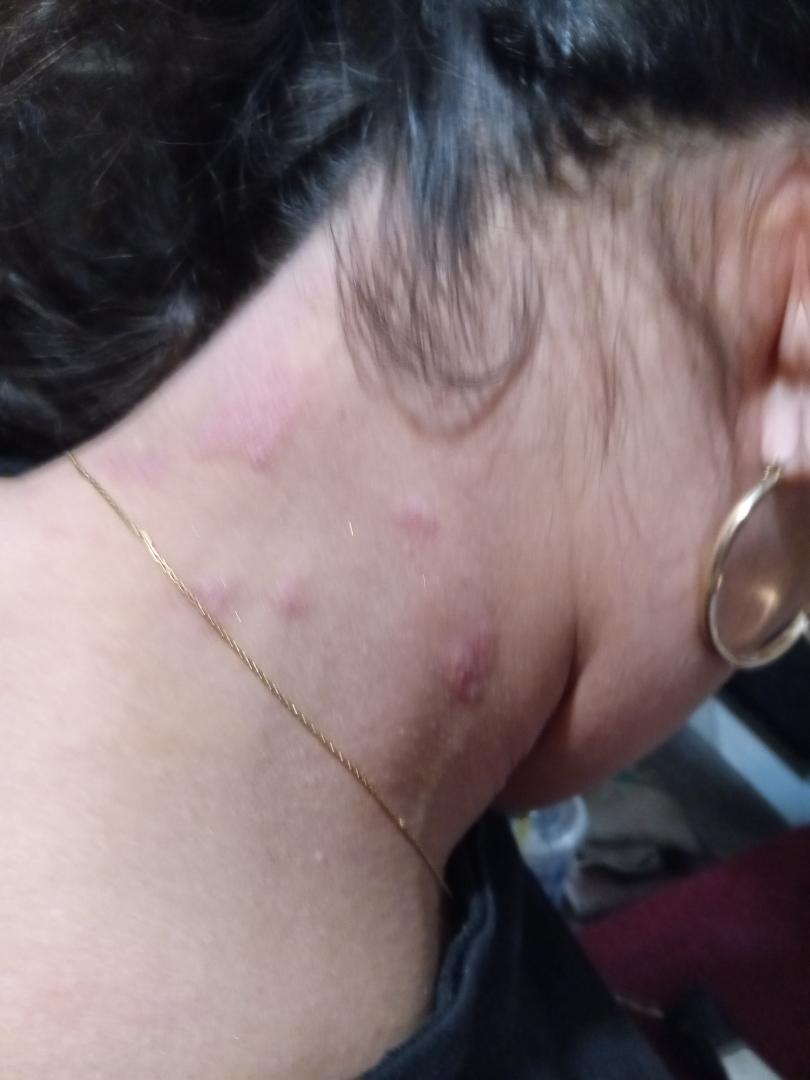Impression: The dermatologist could not determine a likely condition from the photograph alone. History: A close-up photograph.